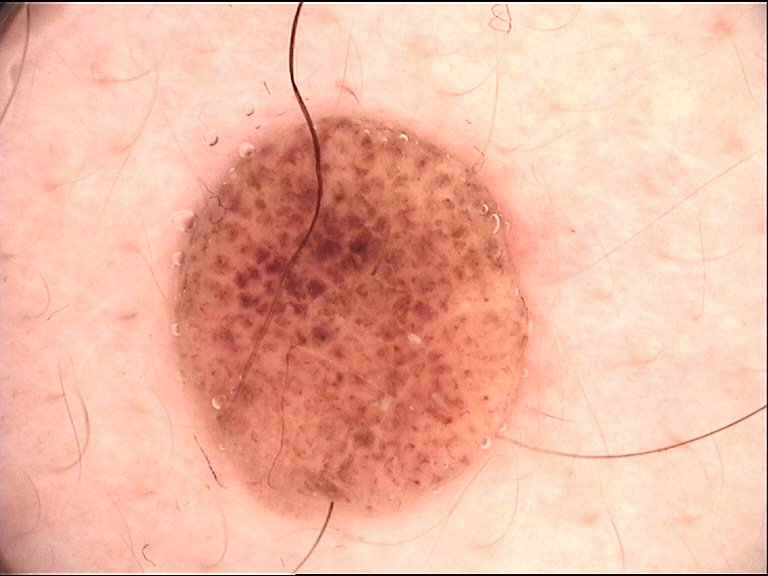image: dermatoscopy
diagnosis:
  name: dermal nevus
  code: db
  malignancy: benign
  super_class: melanocytic
  confirmation: expert consensus